The patient is a male aged around 50, a skin lesion imaged with a dermatoscope.
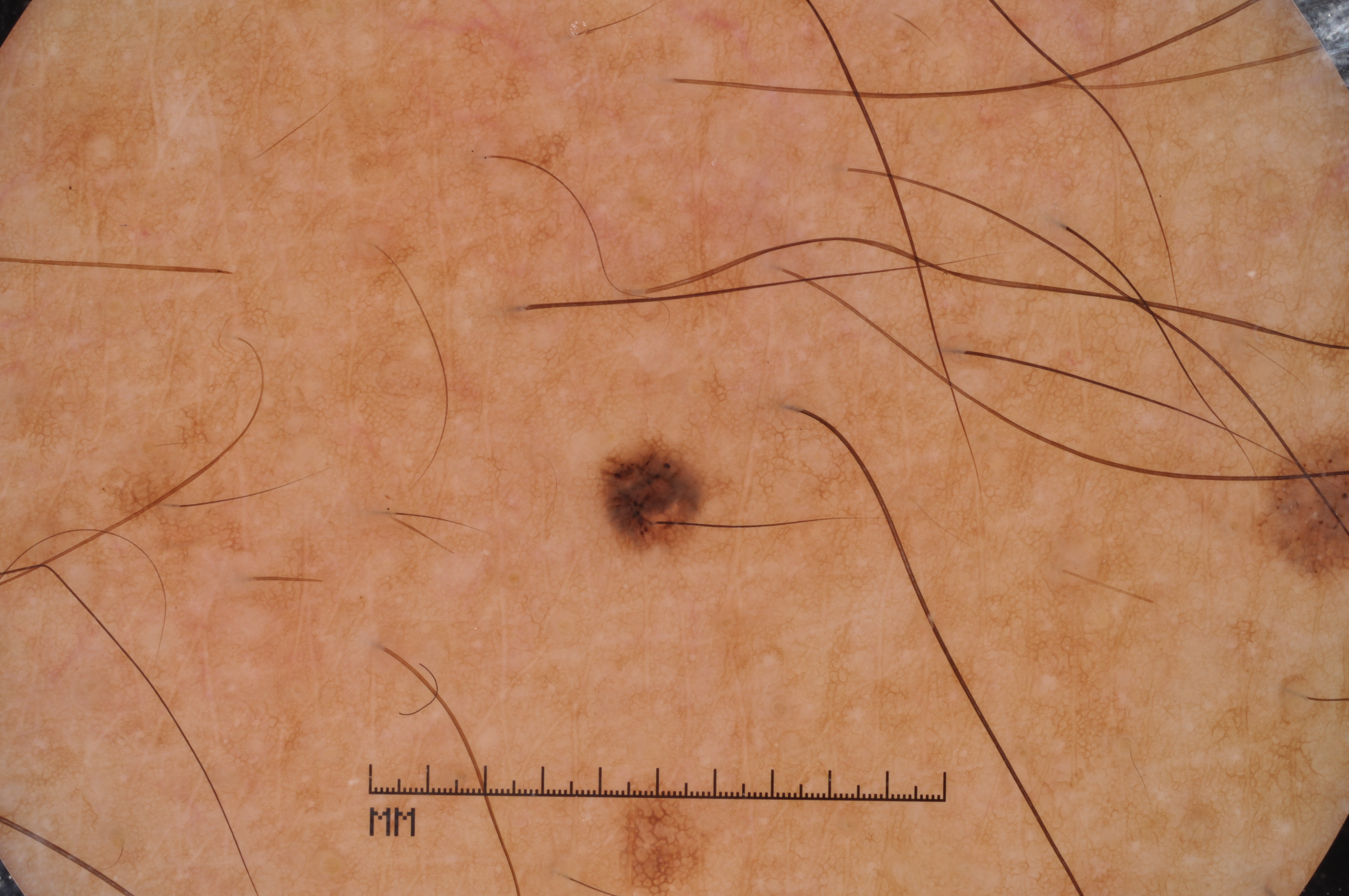The lesion occupies the region bbox(592, 423, 716, 561).
The dermoscopic pattern shows pigment network.
The lesion was assessed as a melanocytic nevus.